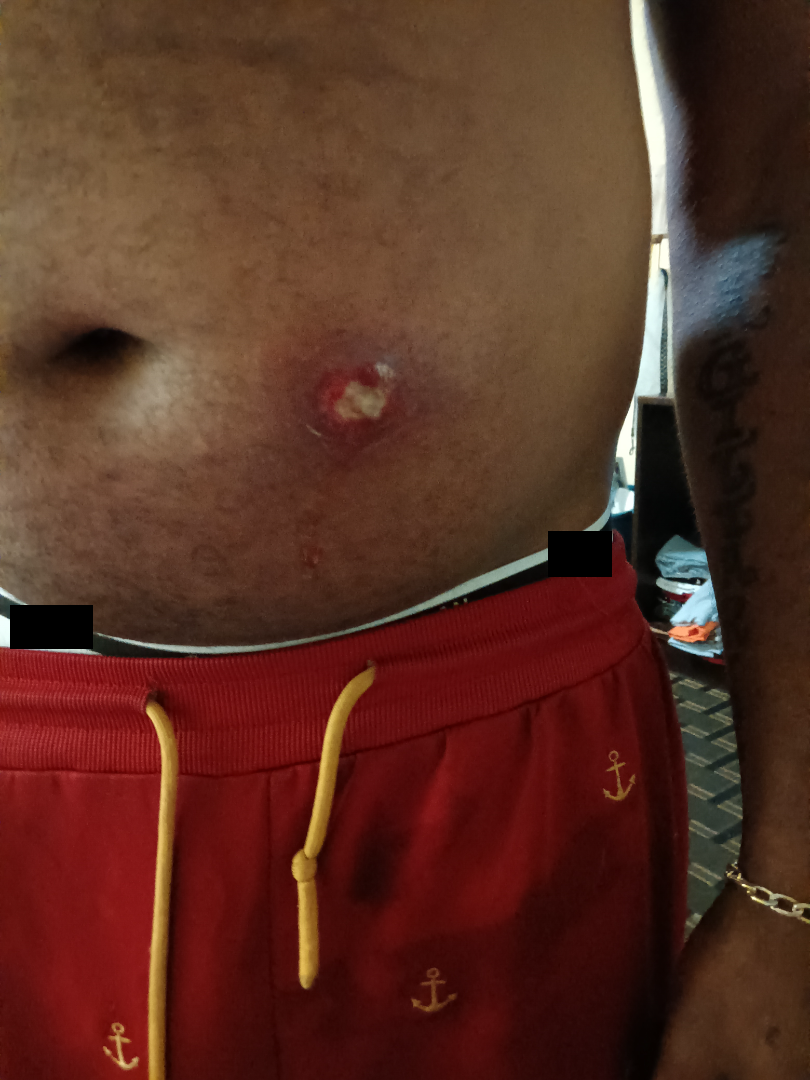assessment=unable to determine | skin tone=Fitzpatrick skin type V; lay reviewers estimated Monk Skin Tone 6 (US pool) or 4 (India pool) | framing=close-up.